A dermoscopy image of a single skin lesion:
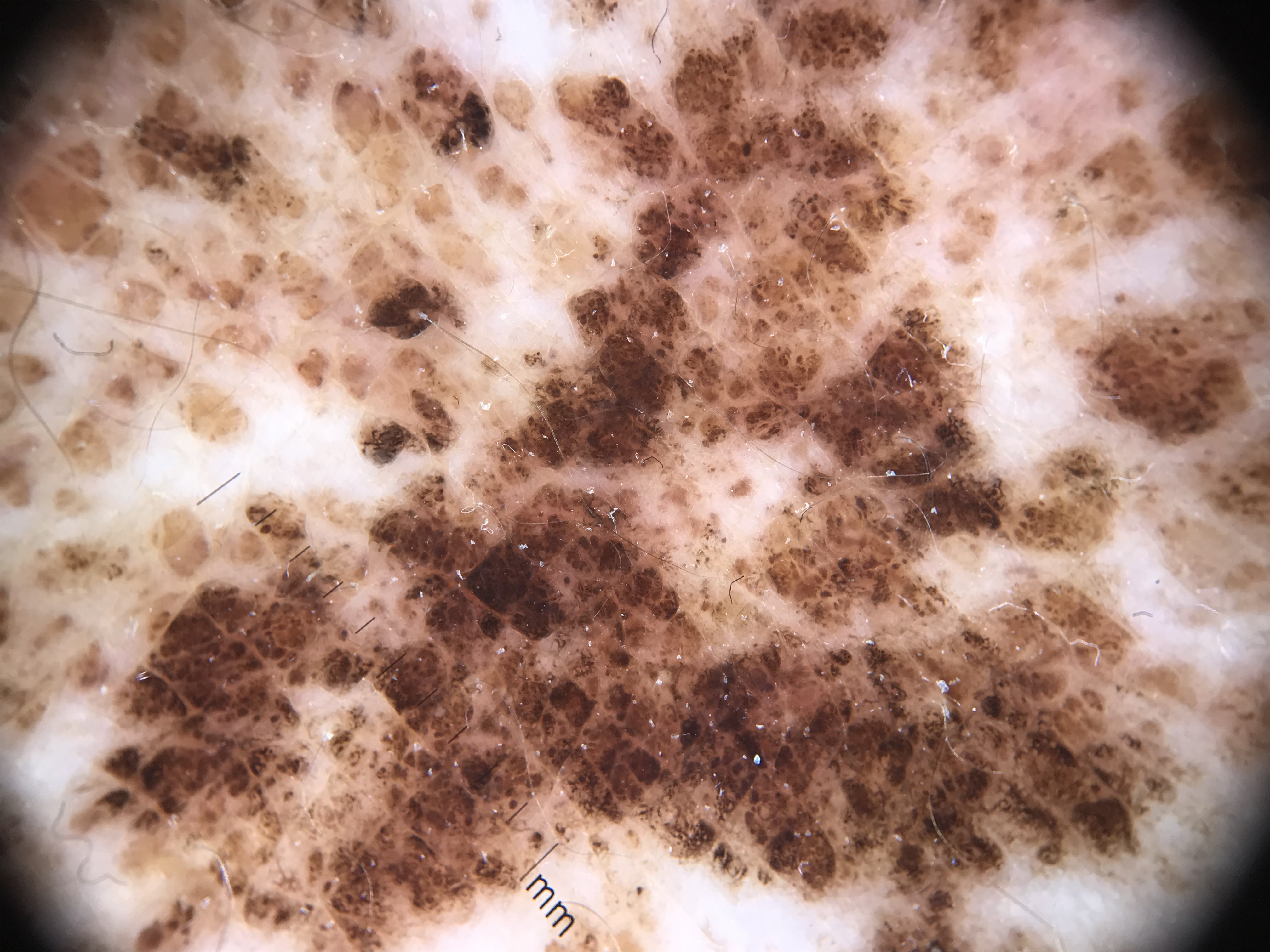  lesion_type:
    main_class: banal
    pattern: junctional
  diagnosis:
    name: congenital junctional nevus
    code: cjb
    malignancy: benign
    super_class: melanocytic
    confirmation: expert consensus